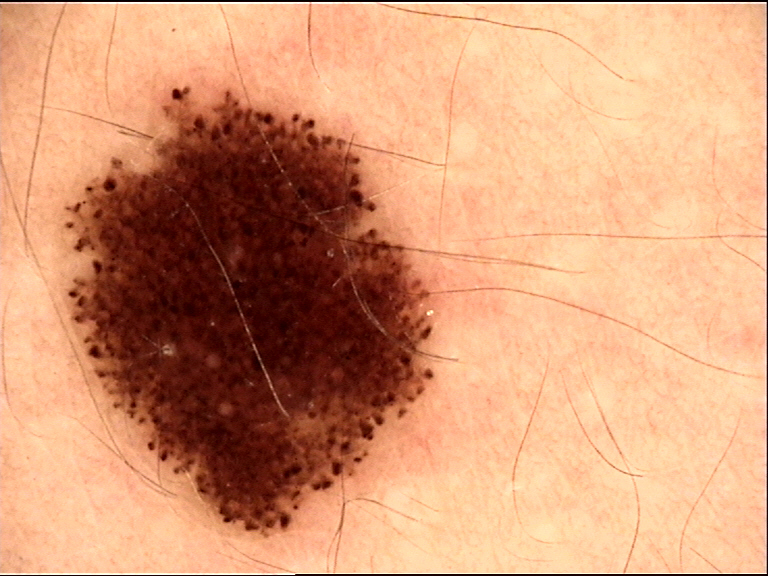Conclusion:
The diagnostic label was a dysplastic compound nevus.